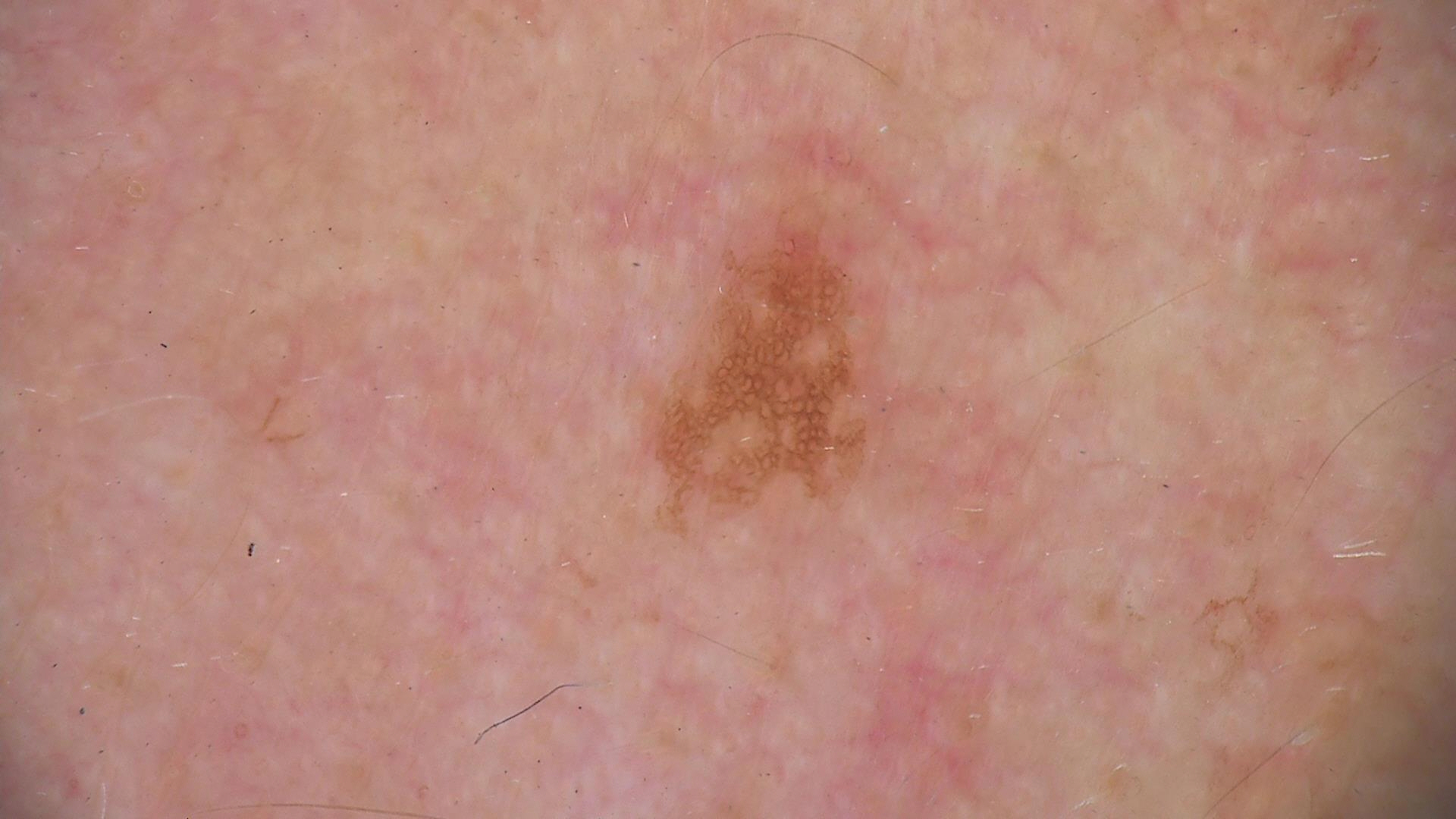| feature | finding |
|---|---|
| modality | dermoscopy |
| category | keratinocytic |
| diagnostic label | seborrheic keratosis (expert consensus) |